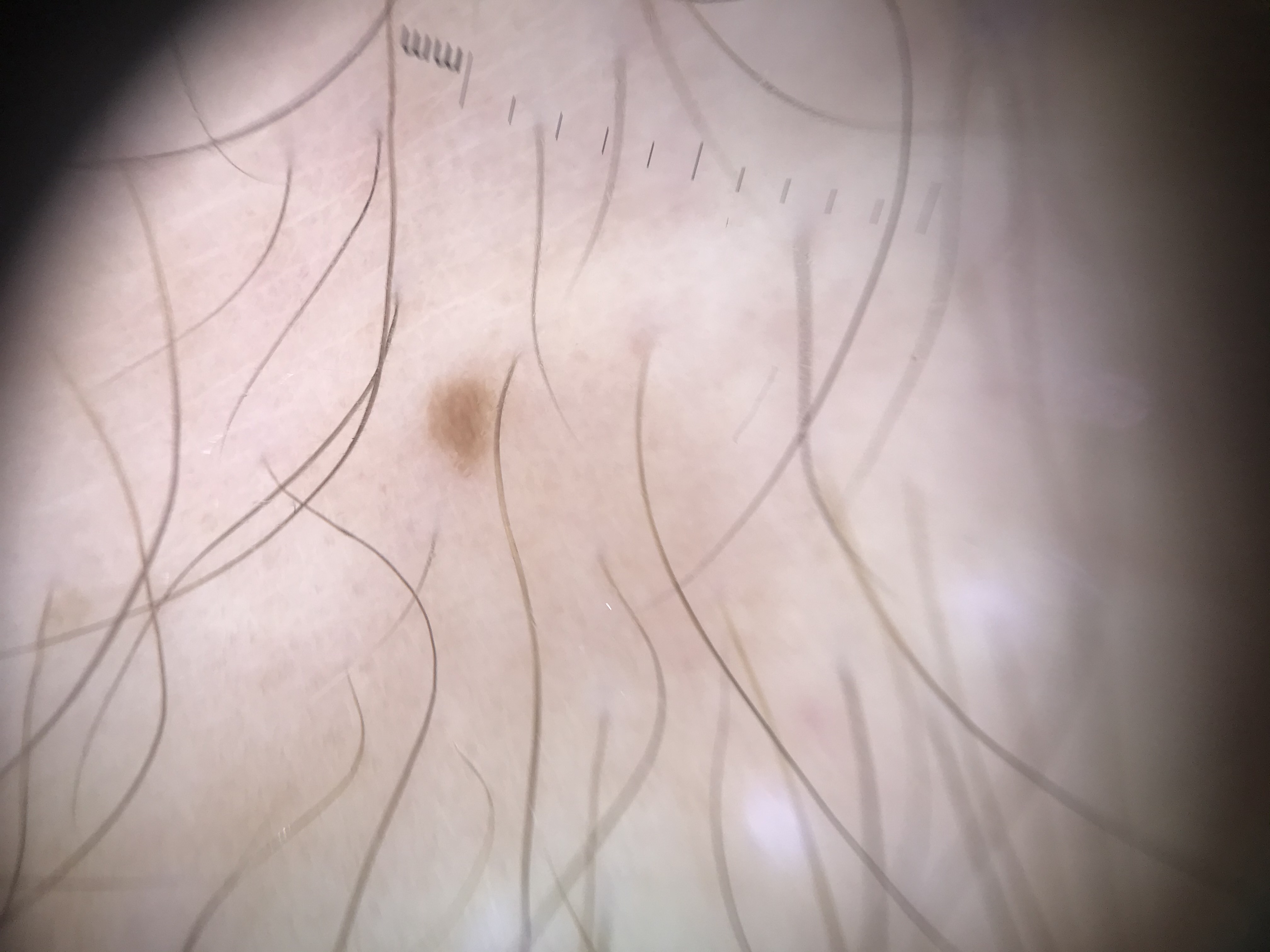Classified as a banal lesion — a junctional nevus.